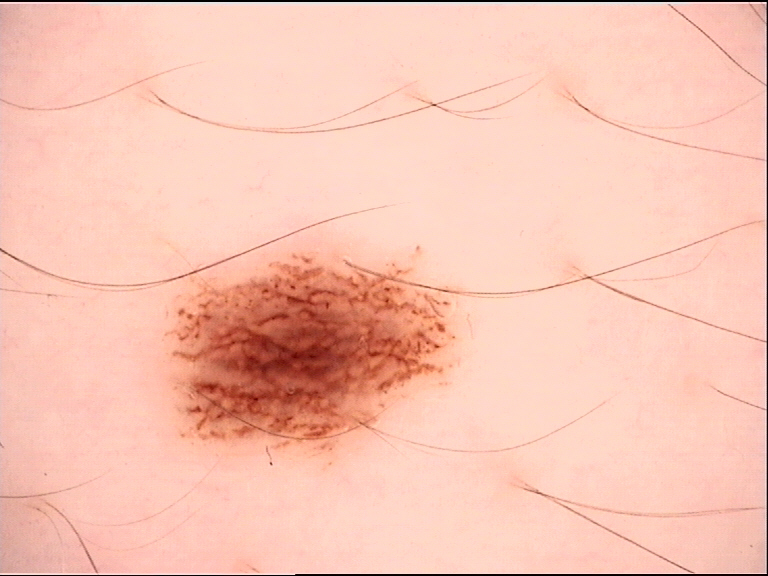imaging: dermatoscopy
diagnostic label: dysplastic junctional nevus (expert consensus)